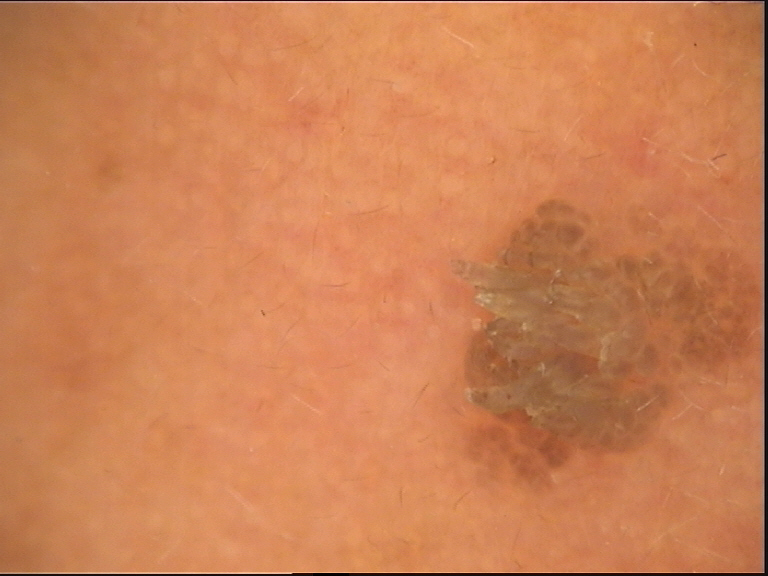diagnostic label = seborrheic keratosis (expert consensus).